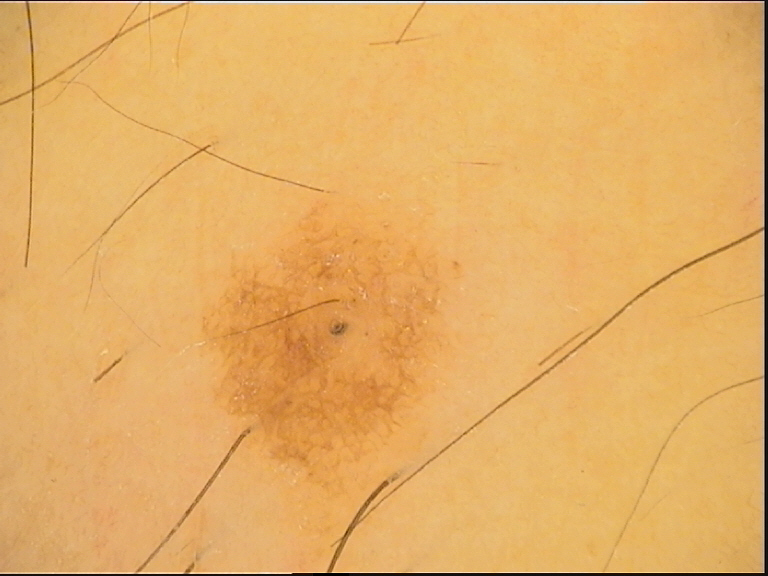{"diagnosis": {"name": "junctional nevus", "code": "jb", "malignancy": "benign", "super_class": "melanocytic", "confirmation": "expert consensus"}}